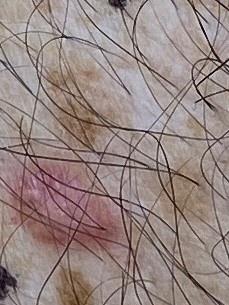diagnostic label: Basal cell carcinoma (biopsy-proven).